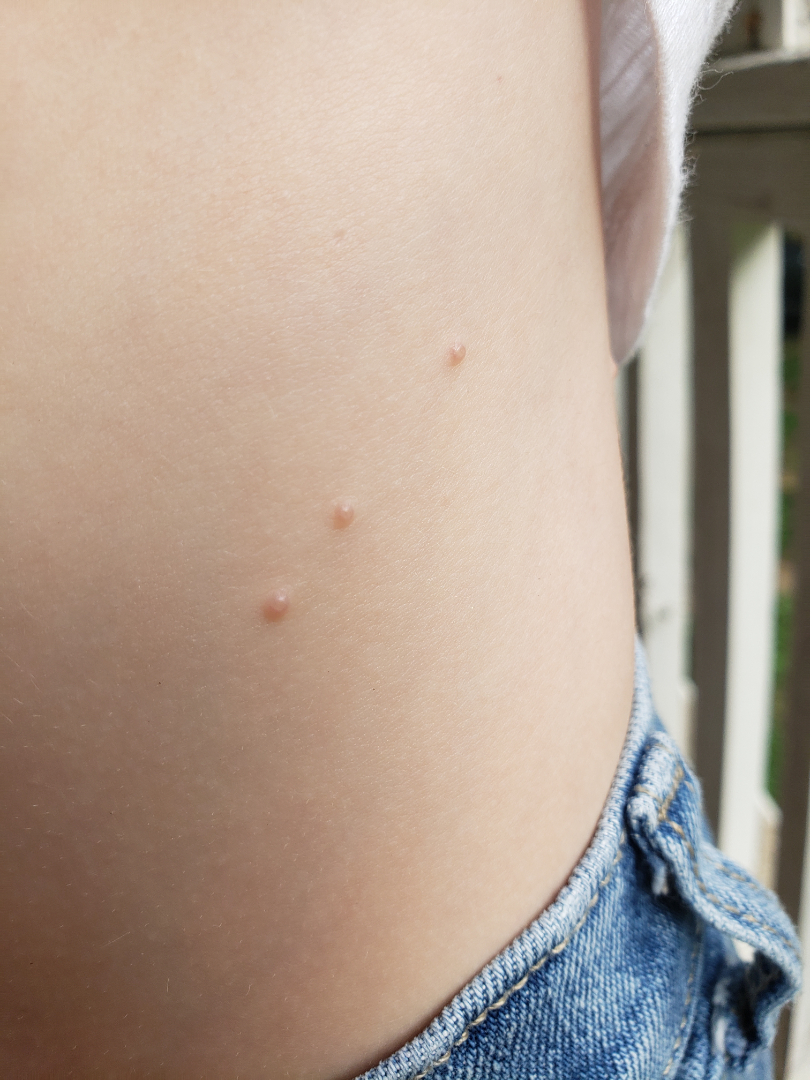Background: Present for more than one year. Fitzpatrick III. The lesion involves the back of the torso and front of the torso. This image was taken at an angle. Findings: Most consistent with Molluscum Contagiosum.